The affected area is the leg, arm and back of the torso · this is a close-up image · the patient is 60–69, female — 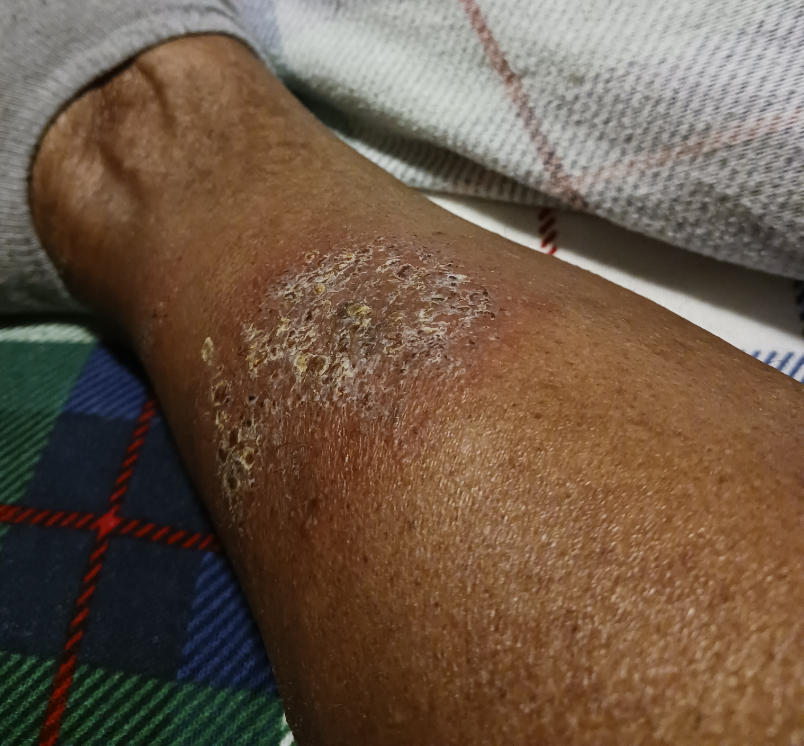<case>
  <differential>
    <leading>Eczema</leading>
    <considered>Stasis Dermatitis</considered>
    <unlikely>Psoriasis</unlikely>
  </differential>
</case>